A dermatoscopic image of a skin lesion: 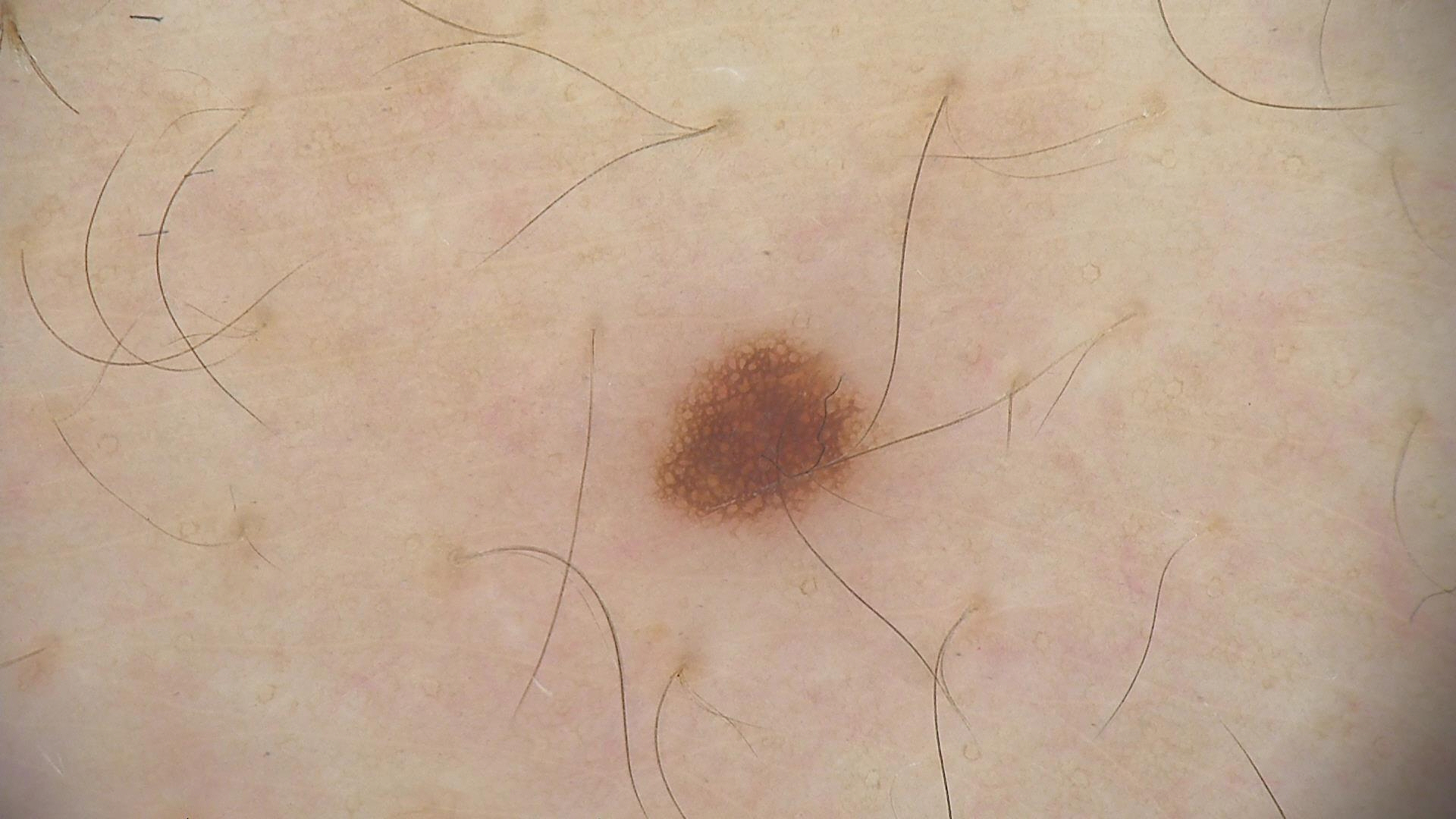Conclusion:
Consistent with a benign lesion — a dysplastic junctional nevus.